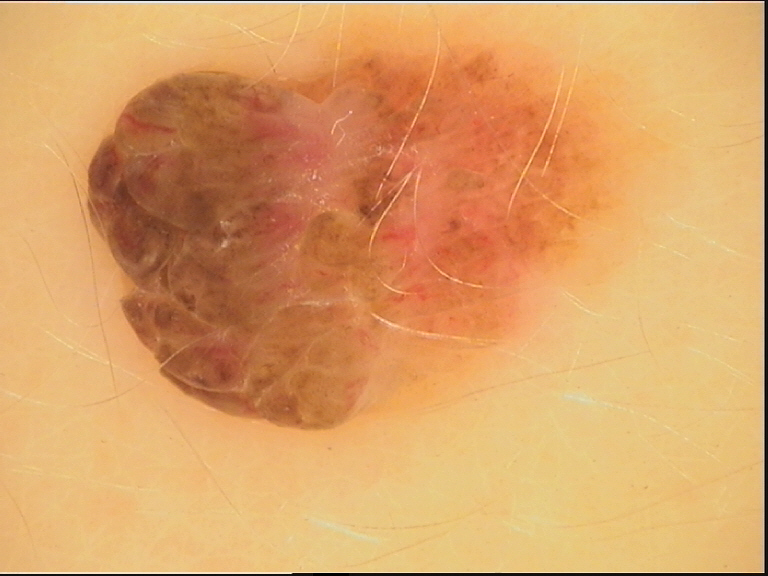Findings:
– diagnosis: dermal nevus (expert consensus)